An image taken at a distance: 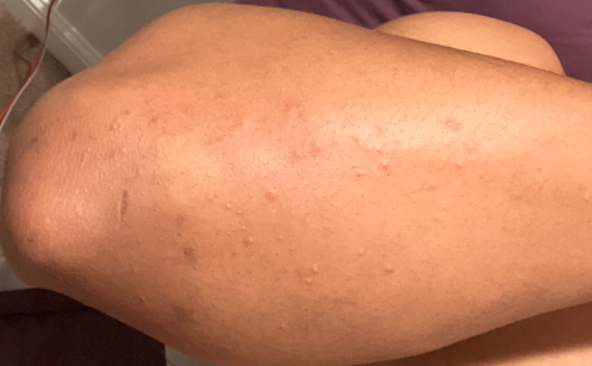Case summary:
– assessment · indeterminate from the photograph